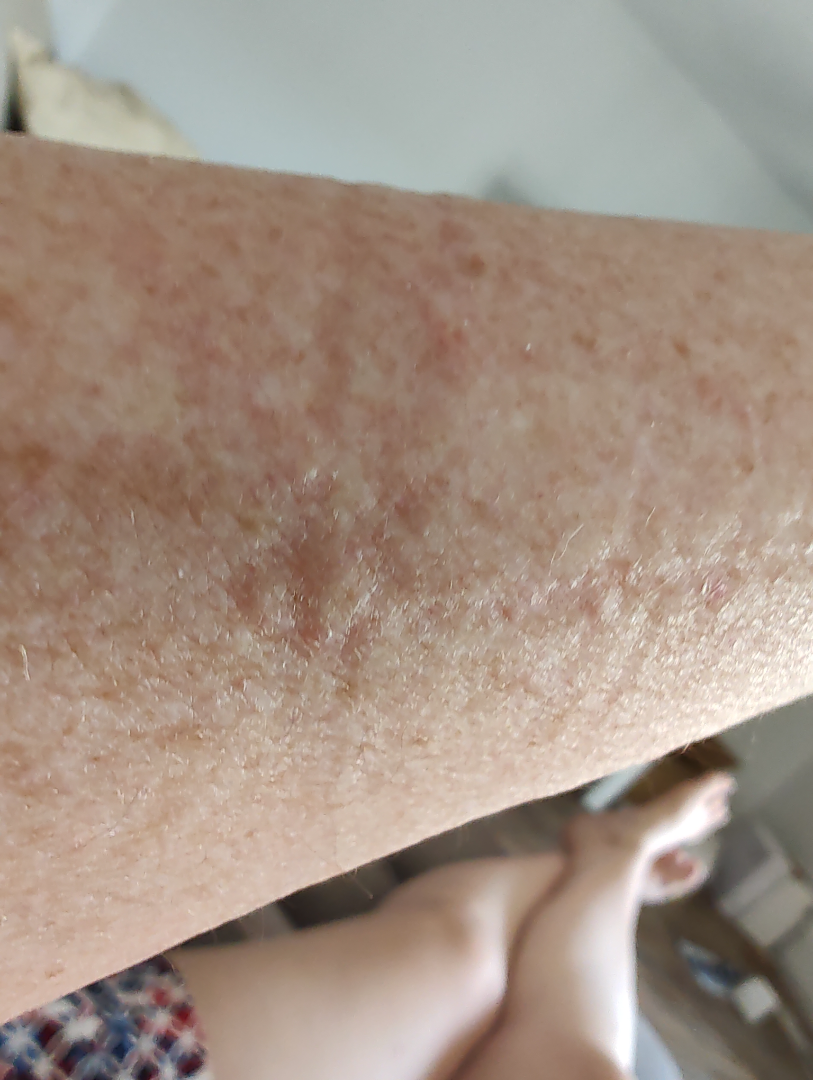The patient considered this a rash. The condition has been present for about one day. No relevant systemic symptoms. Close-up view. The lesion is associated with itching. The affected area is the arm. Female subject, age 60–69. Three independent reviewers: most consistent with Eczema; also raised was Irritant Contact Dermatitis; less likely is Pigmented purpuric eruption; lower on the differential is Allergic Contact Dermatitis.